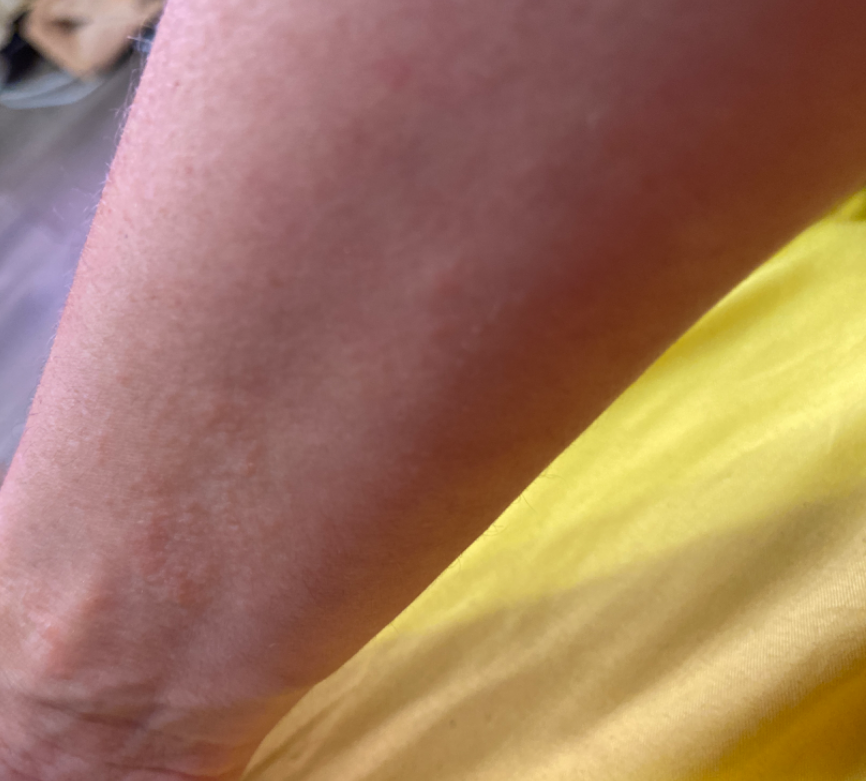Symptoms reported: bothersome appearance. The patient reported no systemic symptoms. Reported duration is about one day. The photo was captured at an angle. Located on the back of the hand and arm. The contributor is 40–49, female. Three dermatologists independently reviewed the case: the leading consideration is Eczema; also raised was Allergic Contact Dermatitis.